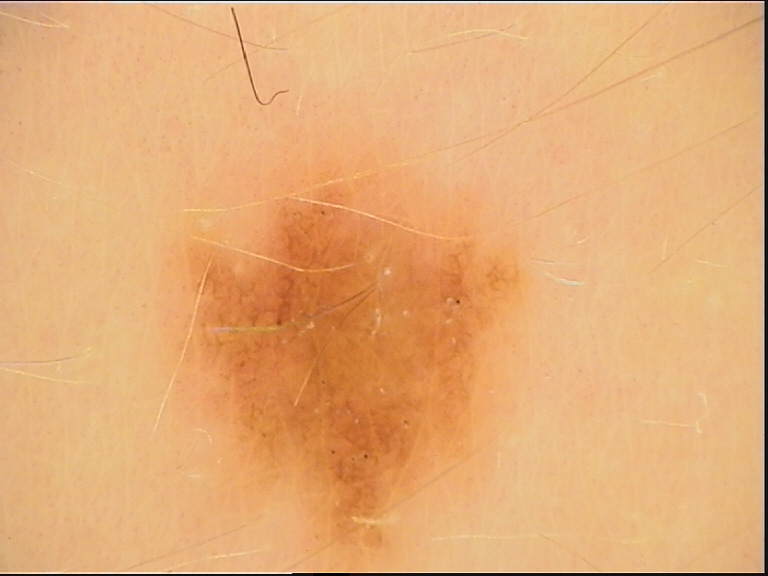Summary: A dermoscopic photograph of a skin lesion. Conclusion: Diagnosed as a dysplastic junctional nevus.